The photo was captured at a distance; the lesion involves the front of the torso — 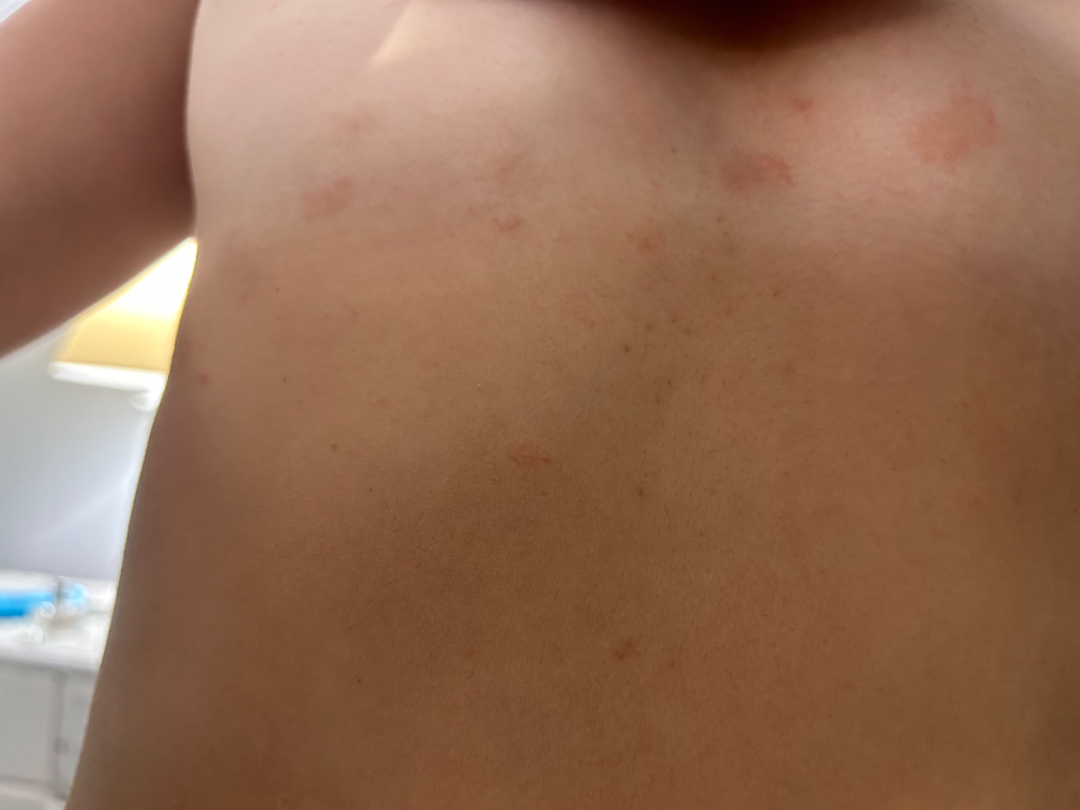Assessment: The skin condition could not be confidently assessed from this image. Clinical context: The condition has been present for one to four weeks. The contributor notes bothersome appearance.